A female patient age 59:
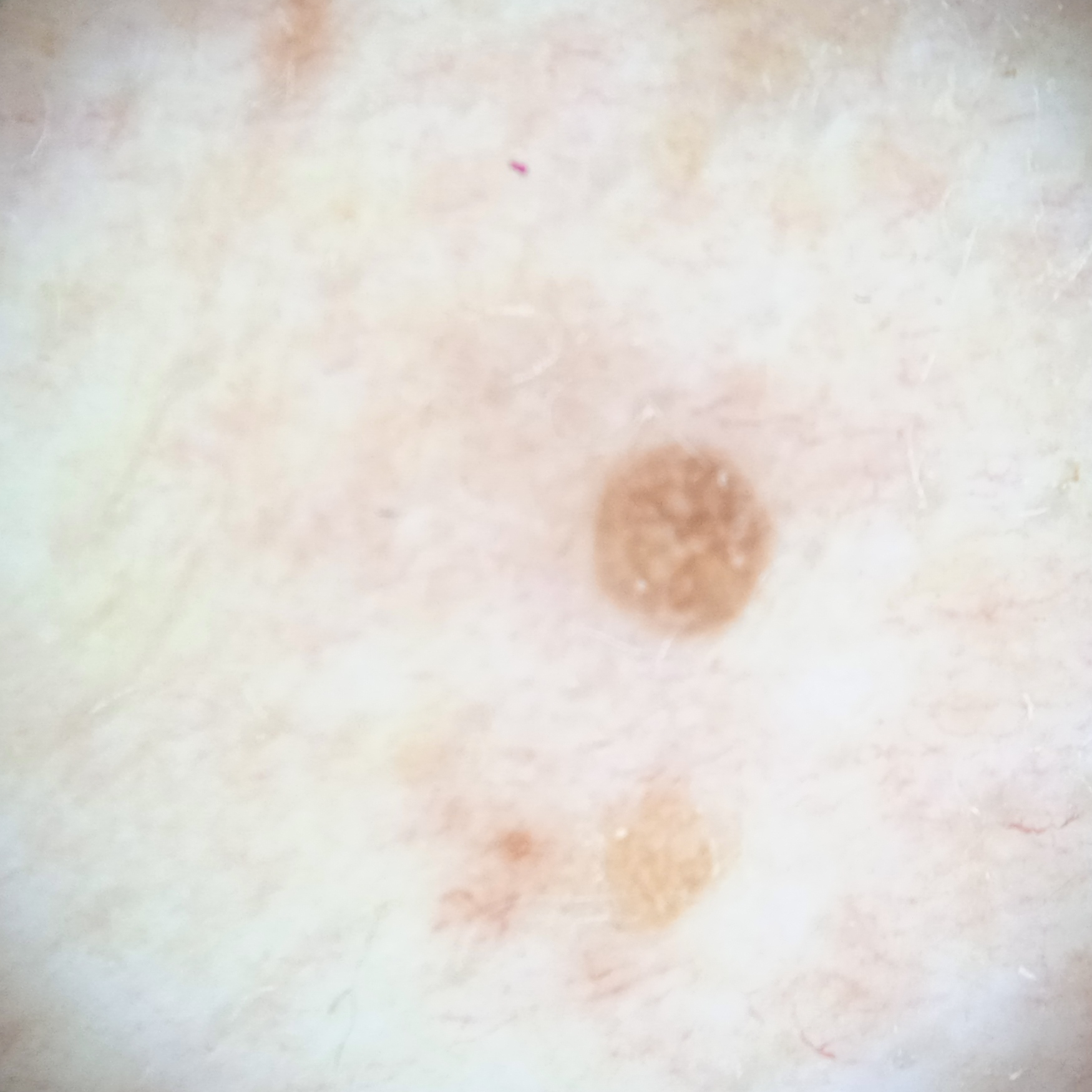site=the torso | diagnostic label=seborrheic keratosis (dermatologist consensus).